A dermatoscopic image of a skin lesion. A female patient age 55. The patient describes having a moderate number of moles. By self-report, a prior organ transplant and immunosuppression.
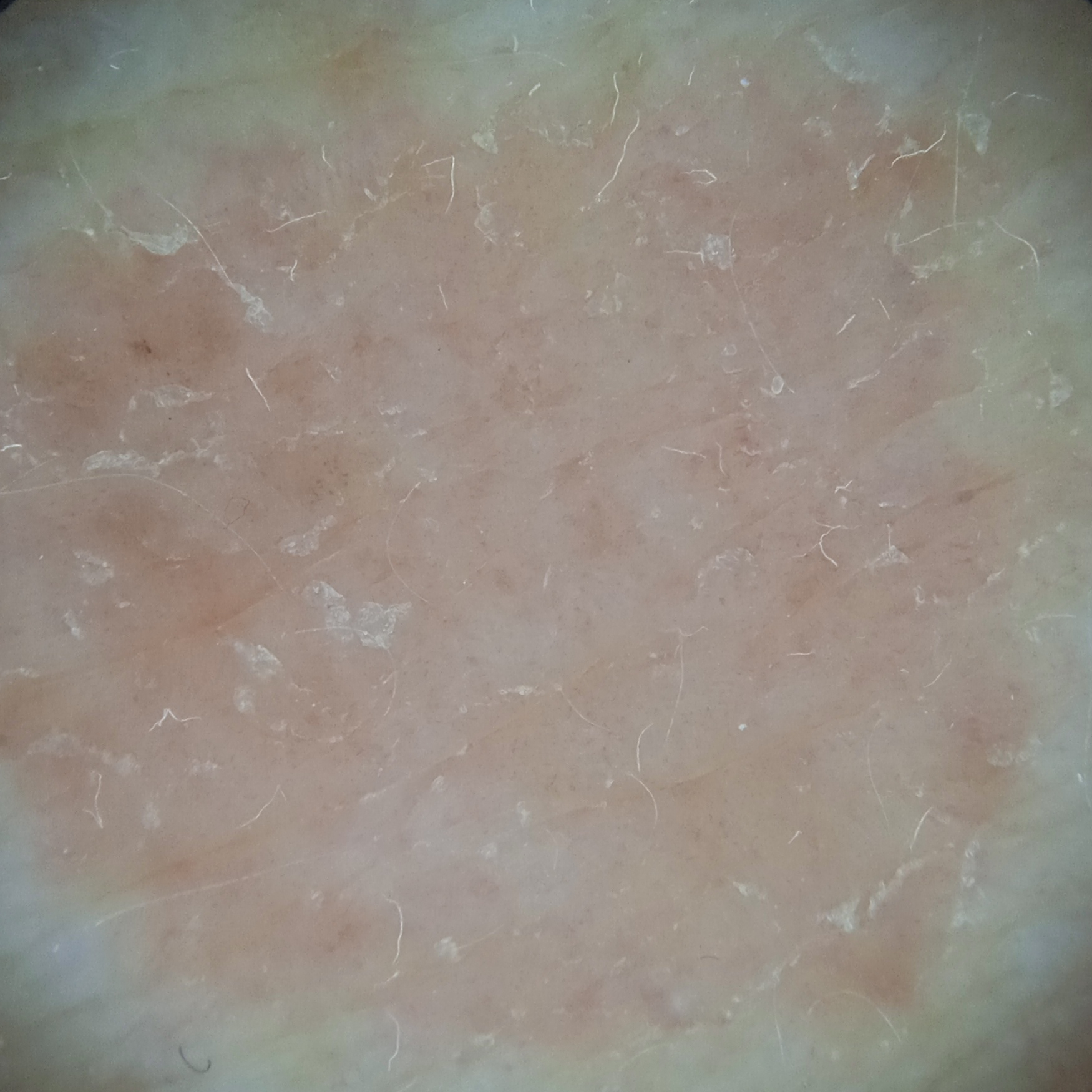Q: Lesion size?
A: 13.2 mm
Q: What was the diagnosis?
A: basal cell carcinoma (dermatologist consensus)